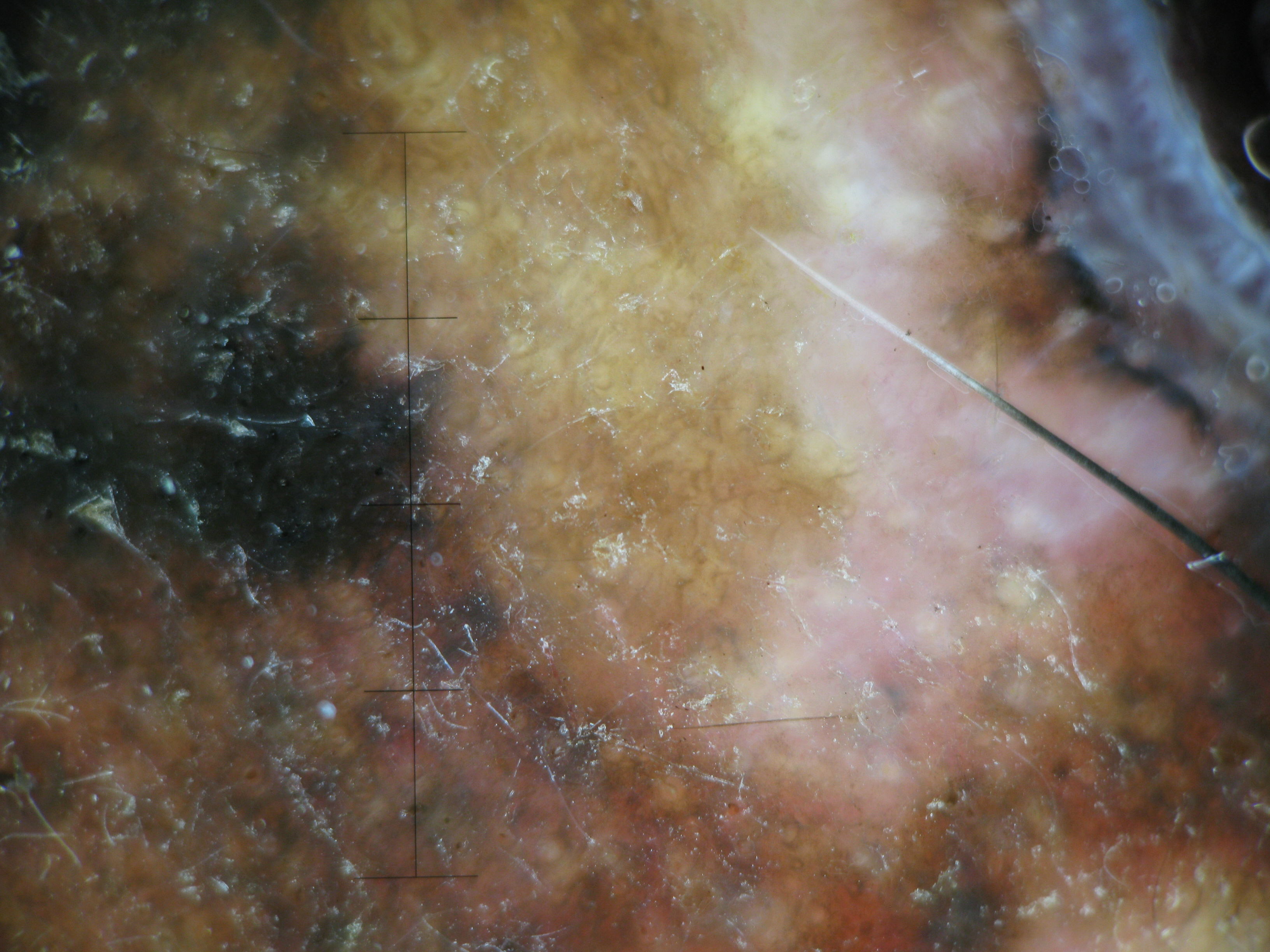A skin lesion imaged with a dermatoscope.
Histopathology confirmed a lentigo maligna melanoma.